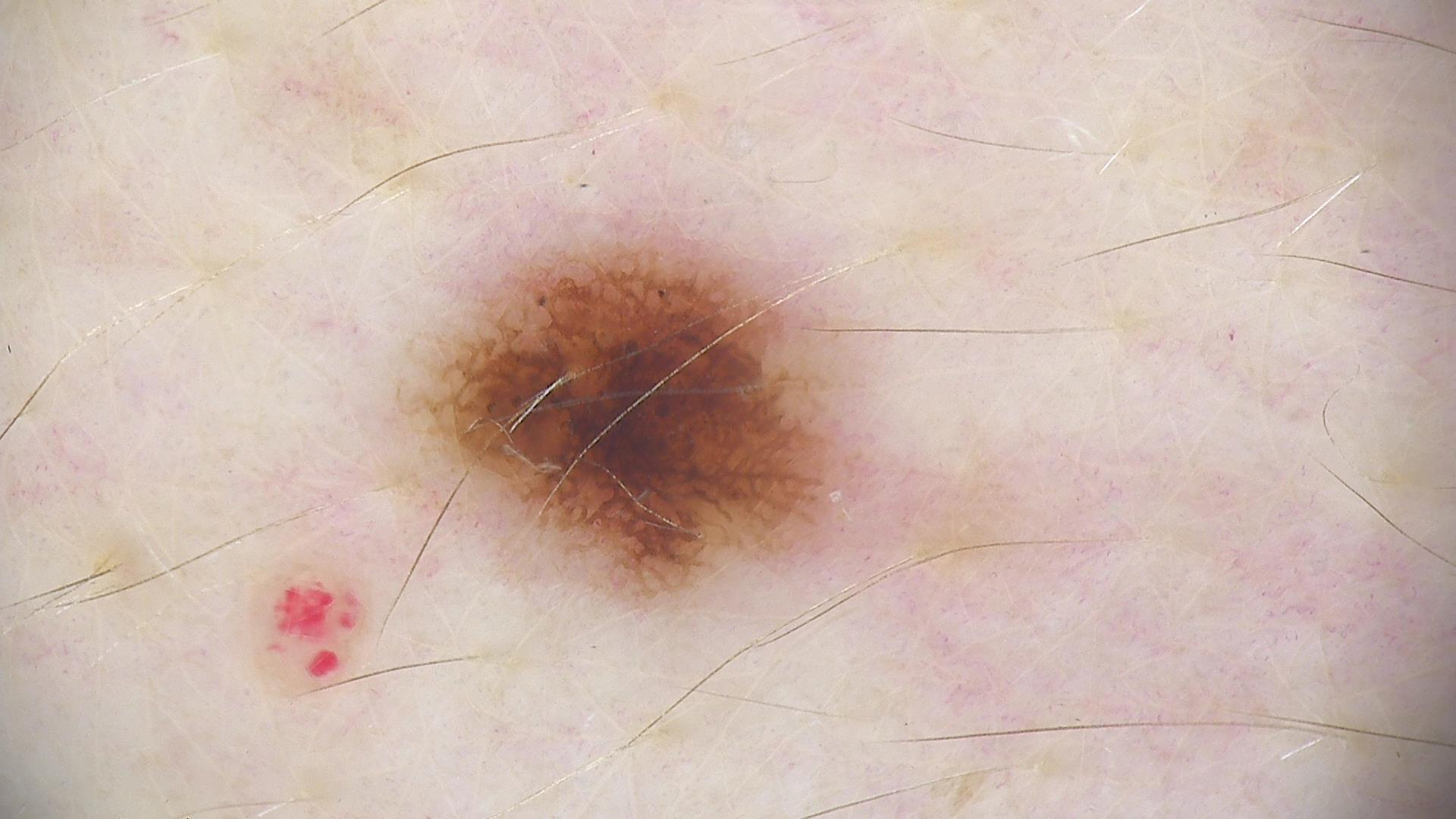Labeled as a dysplastic junctional nevus.